The patient describes having a moderate number of moles · a skin lesion imaged with a dermatoscope · acquired for a research image collection, with no referral diagnosis · a female subject age 50: 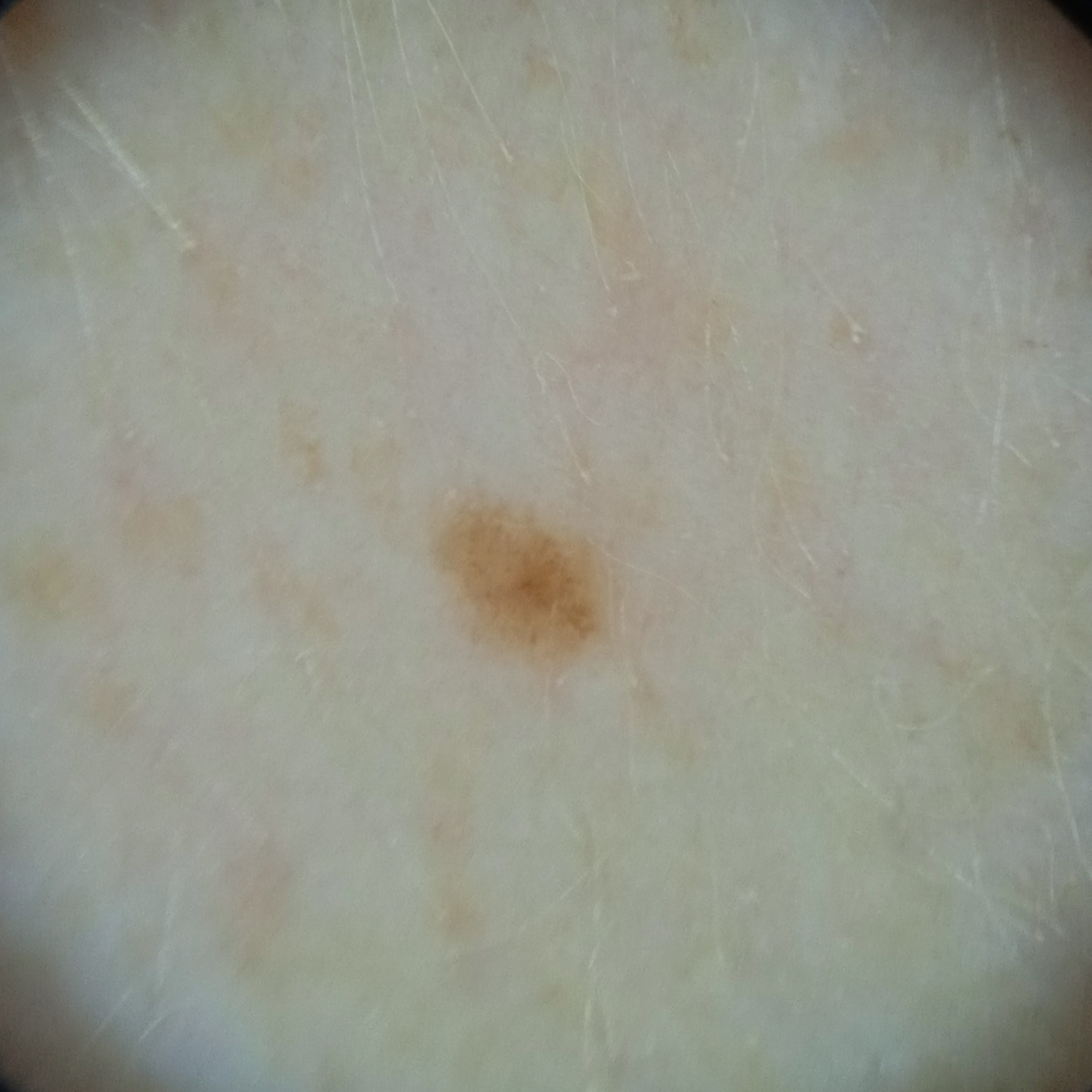Summary: The lesion is on an arm. The lesion is about 2 mm across. Impression: The lesion was assessed as a melanocytic nevus.